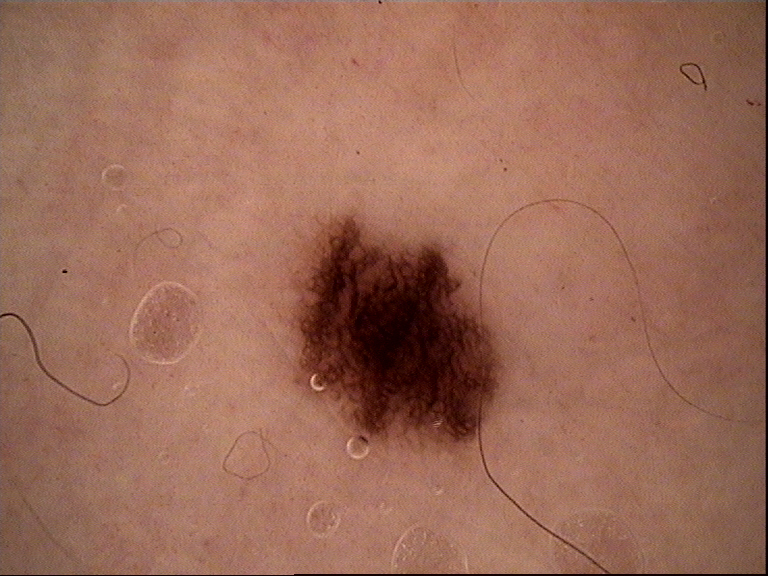Classified as a dysplastic junctional nevus.